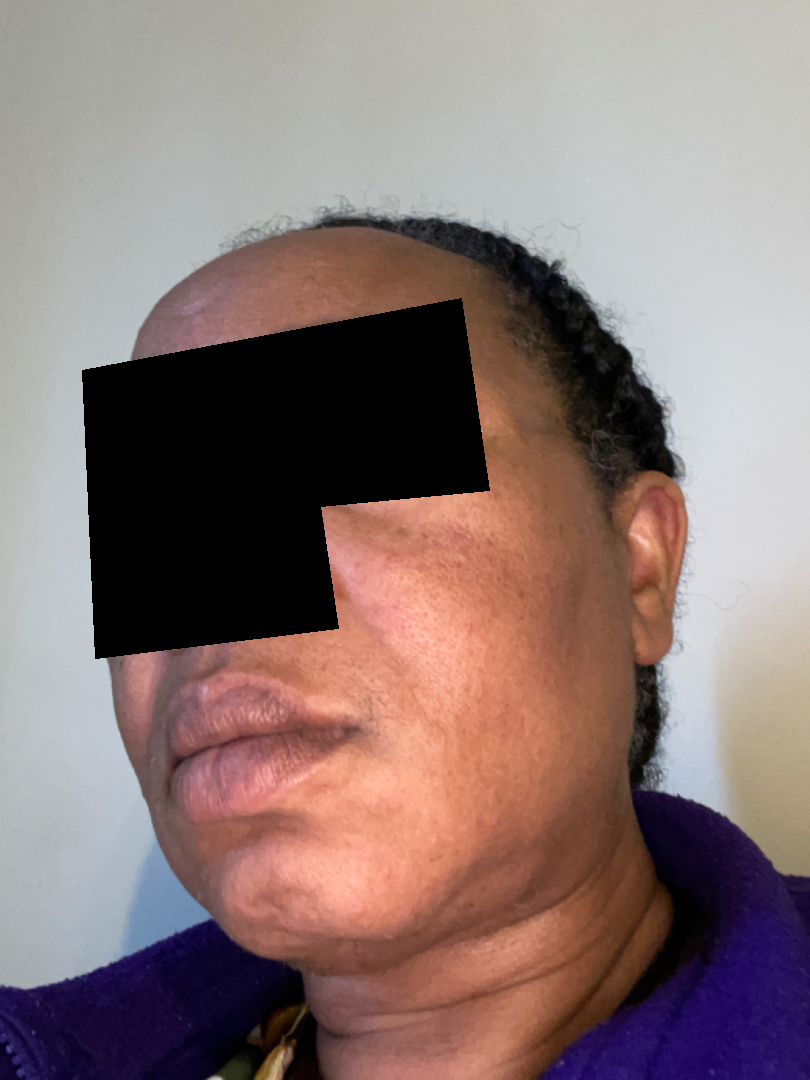The skin condition could not be confidently assessed from this image.
The photograph was taken at an angle.